A dermoscopy image of a single skin lesion:
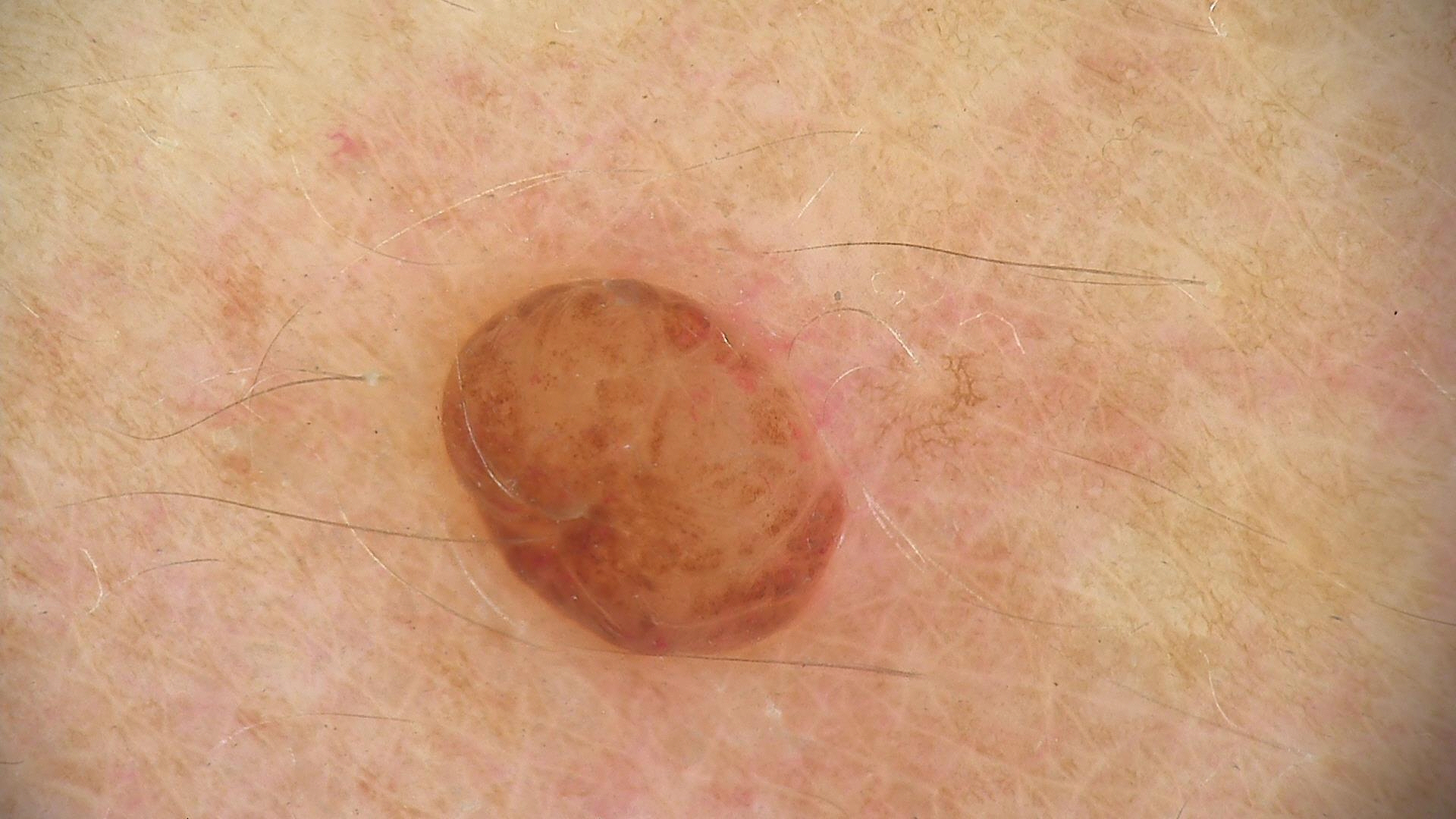category=banal
diagnostic label=dermal nevus (expert consensus)